Dermoscopy of a skin lesion.
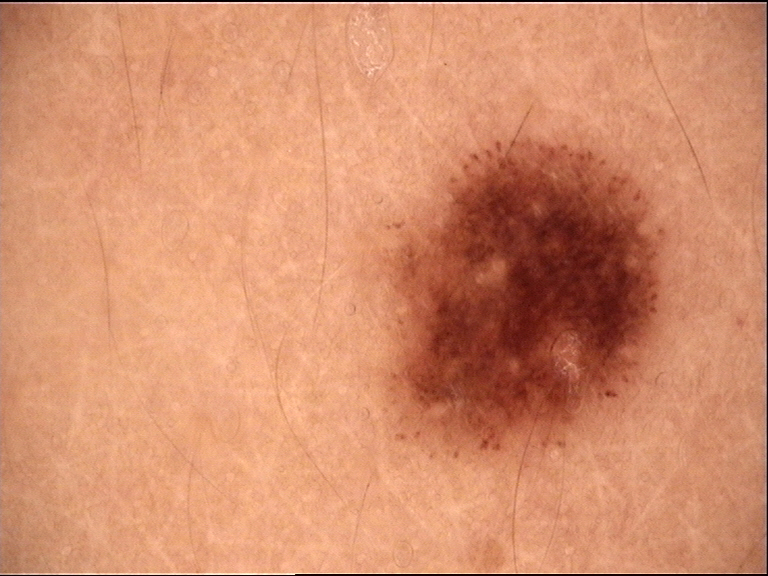assessment: dysplastic junctional nevus (expert consensus).